The lesion involves the leg · the contributor notes the condition has been present for about one day · a close-up photograph · the lesion is described as raised or bumpy · self-categorized by the patient as skin that appeared healthy to them:
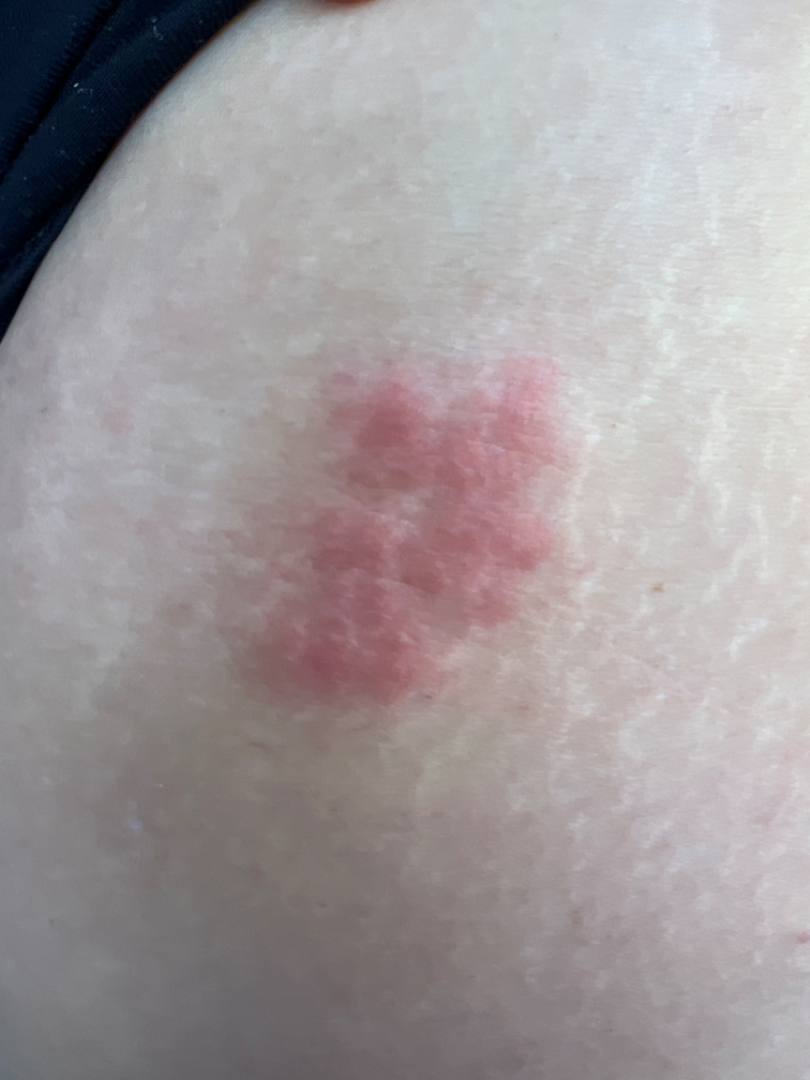Case summary:
* assessment — not assessable